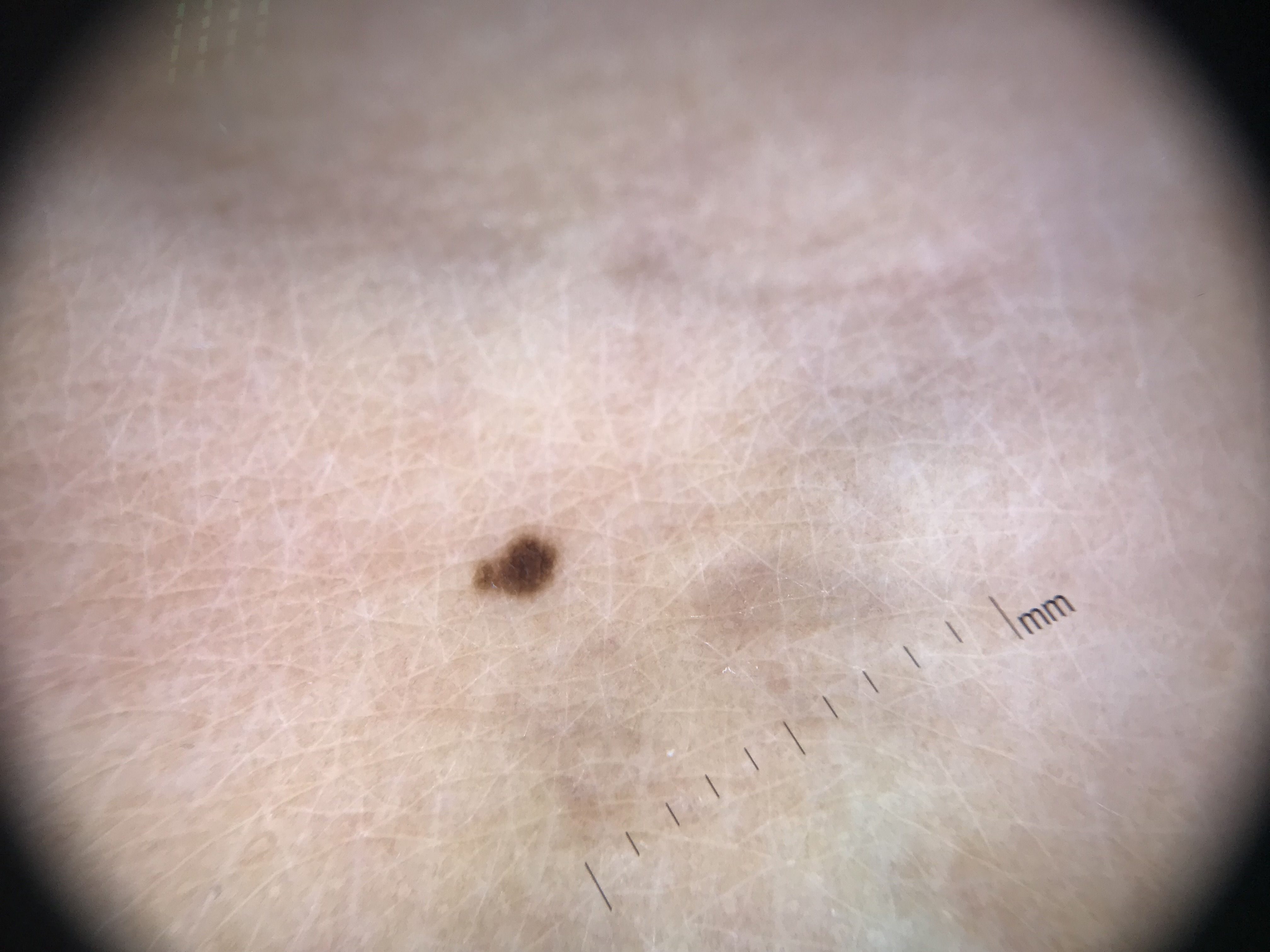<dermoscopy>
  <image>dermatoscopy</image>
  <lesion_type>
    <main_class>banal</main_class>
    <pattern>junctional</pattern>
  </lesion_type>
  <diagnosis>
    <name>junctional nevus</name>
    <code>jb</code>
    <malignancy>benign</malignancy>
    <super_class>melanocytic</super_class>
    <confirmation>expert consensus</confirmation>
  </diagnosis>
</dermoscopy>